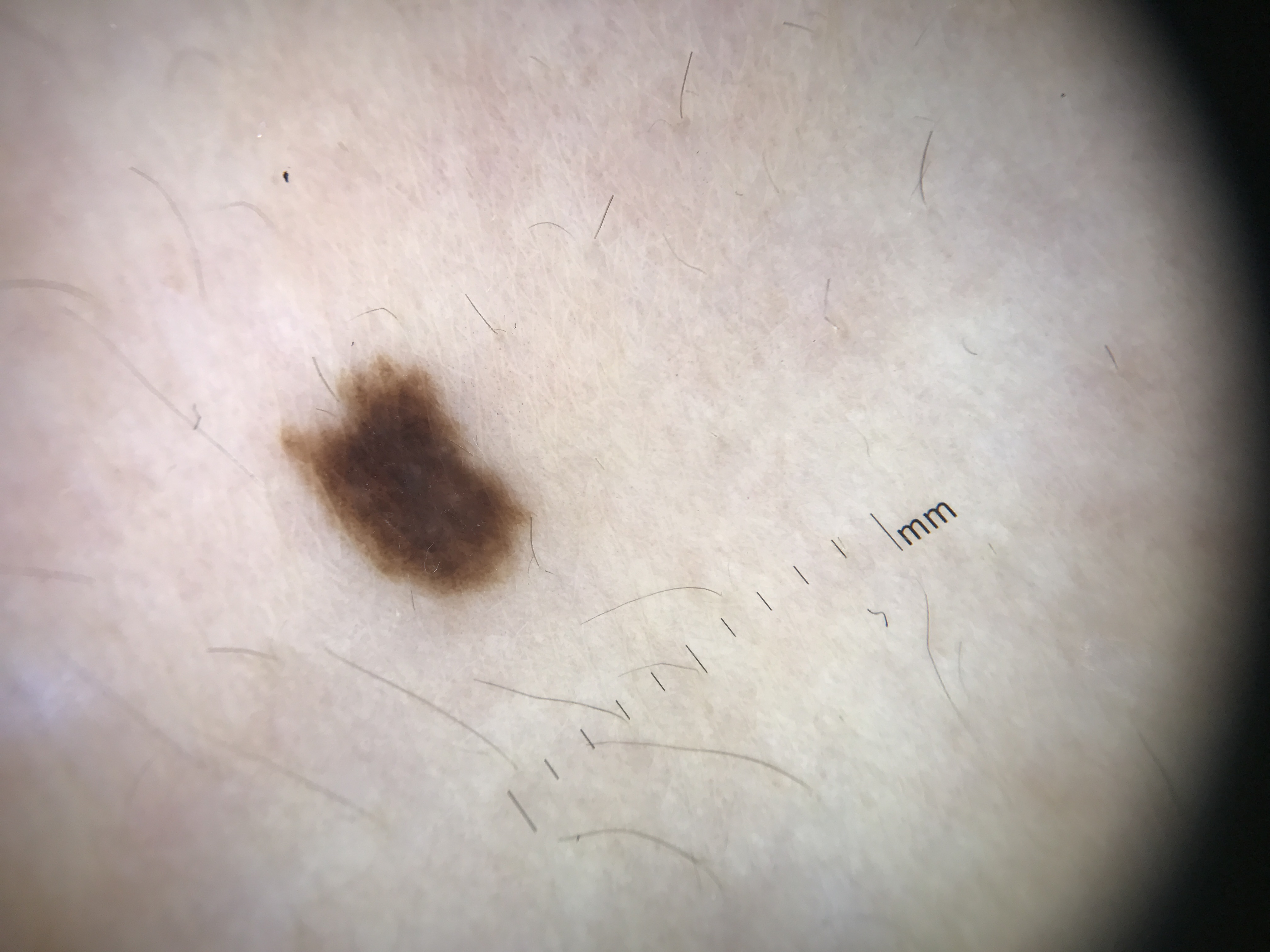diagnosis = dysplastic junctional nevus (expert consensus).